A dermoscopic image of a skin lesion.
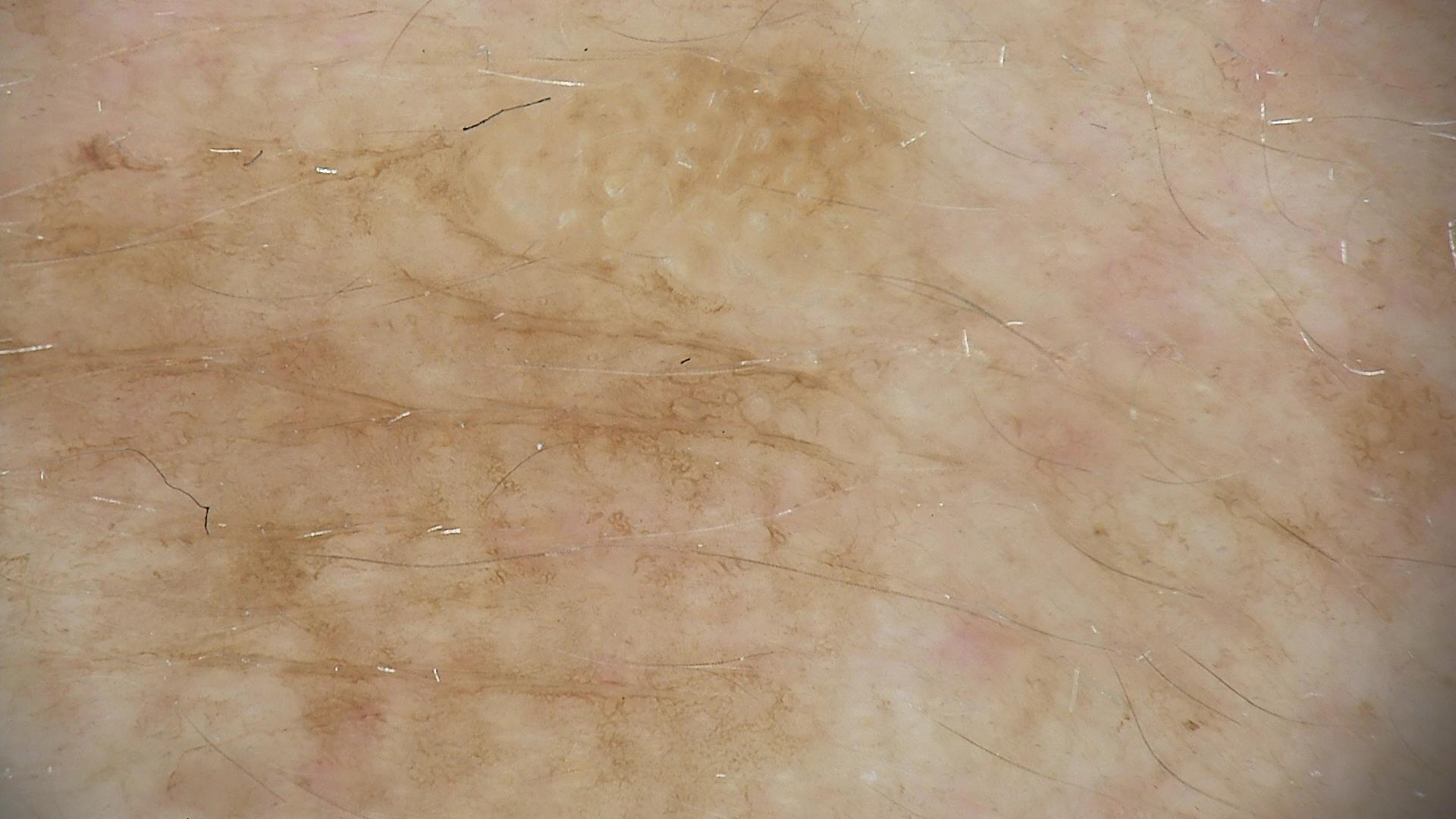Summary:
The architecture is that of a keratinocytic lesion.
Conclusion:
Classified as a seborrheic keratosis.